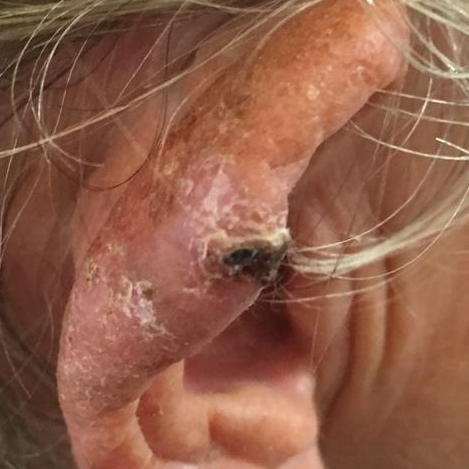<skin_lesion>
  <patient>
    <age>71</age>
    <gender>female</gender>
  </patient>
  <image>clinical photograph</image>
  <skin_type>II</skin_type>
  <lesion_size>
    <diameter_1_mm>20.0</diameter_1_mm>
    <diameter_2_mm>10.0</diameter_2_mm>
  </lesion_size>
  <diagnosis>
    <name>basal cell carcinoma</name>
    <code>BCC</code>
    <malignancy>malignant</malignancy>
    <confirmation>histopathology</confirmation>
  </diagnosis>
</skin_lesion>